The patient is Fitzpatrick skin type I; a male patient roughly 75 years of age; the chart records a prior melanoma but no first-degree relative with melanoma:
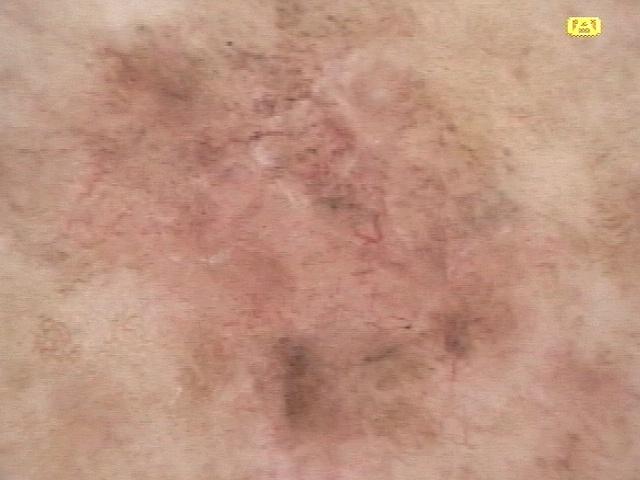The lesion was found on the posterior trunk. Confirmed on histopathology as a nevus.